A skin lesion imaged with a dermatoscope:
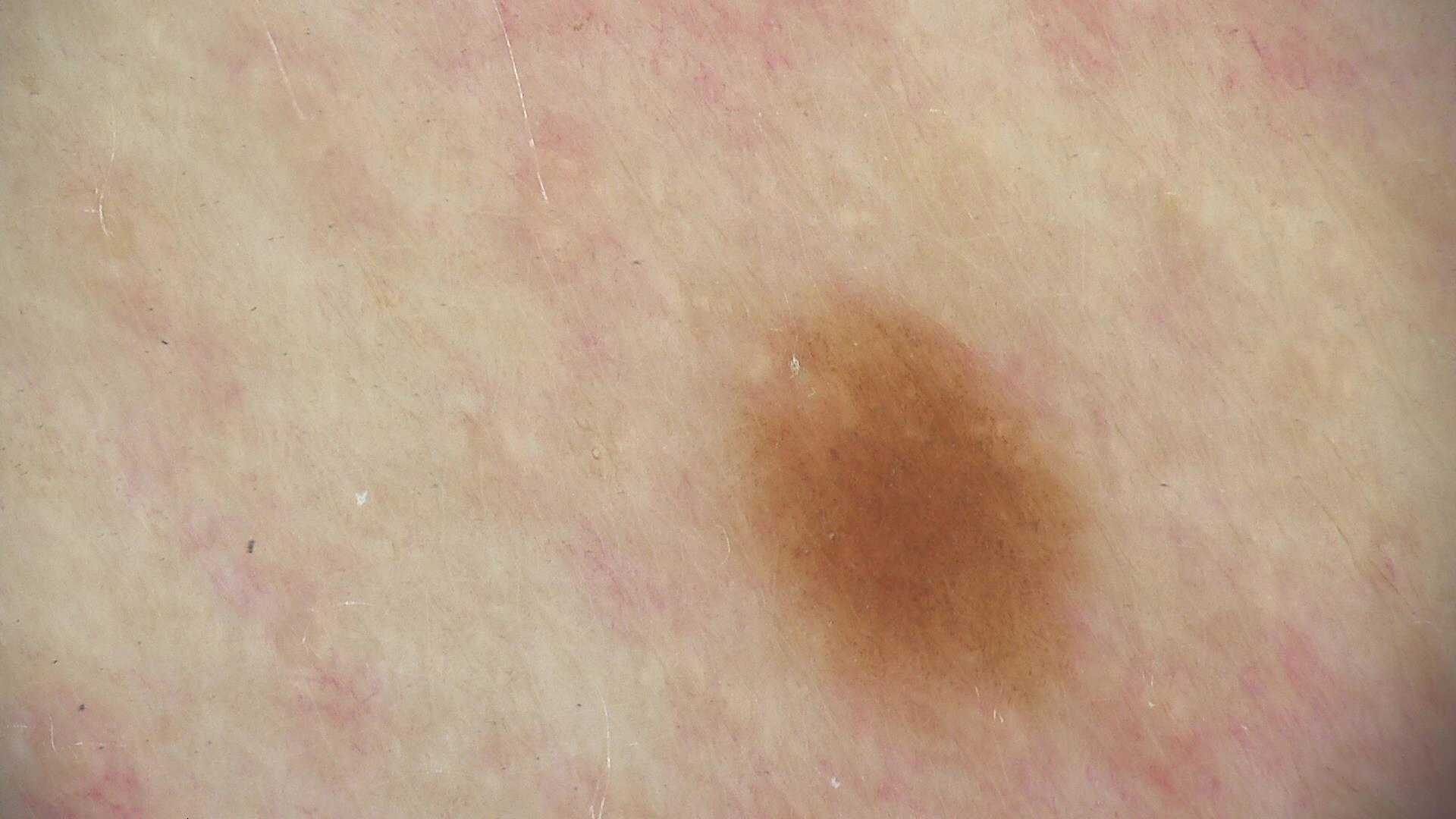label: junctional nevus (expert consensus).